A skin lesion imaged with a dermatoscope:
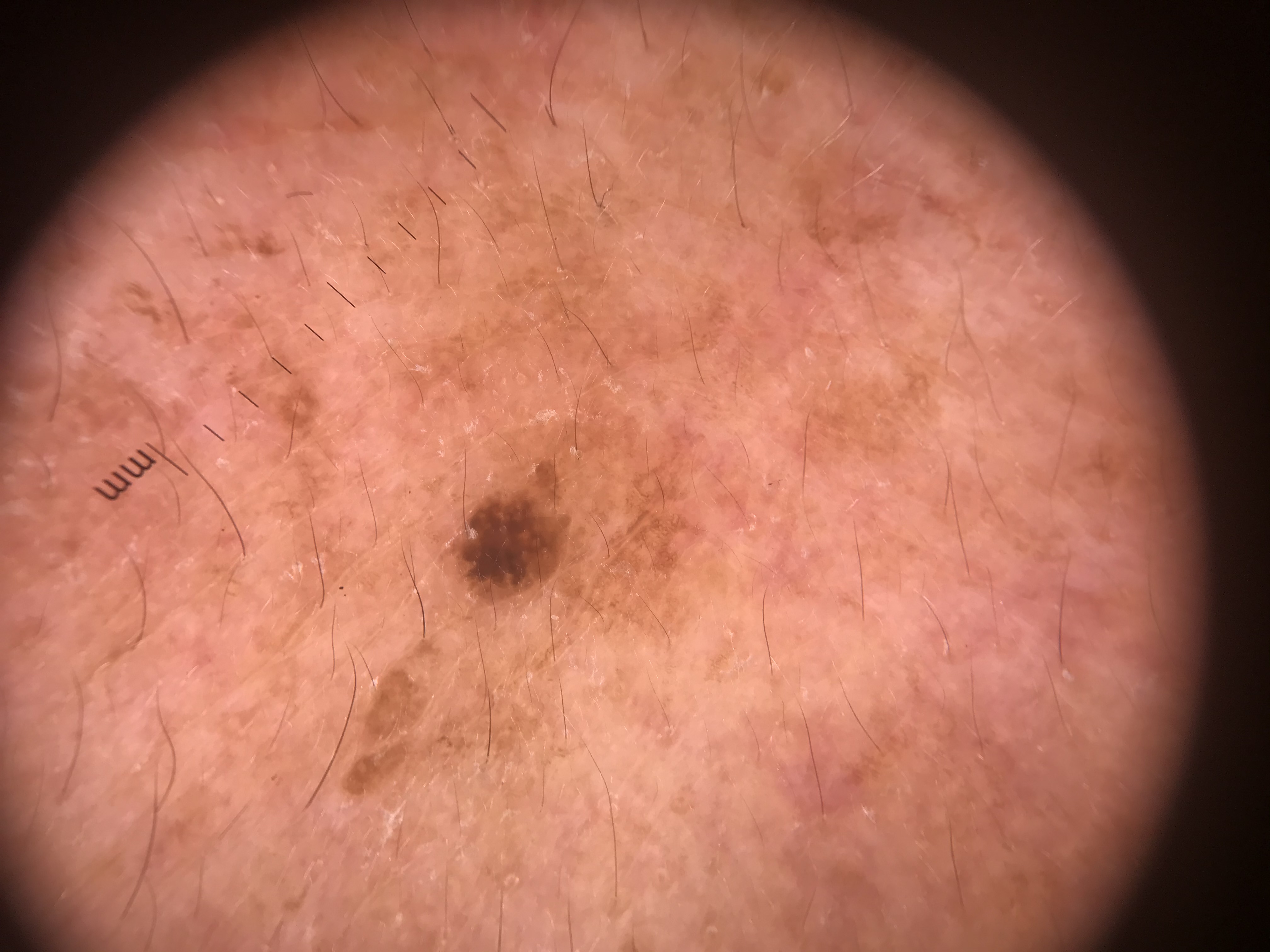This is a keratinocytic lesion. Labeled as a seborrheic keratosis.